The arm and leg are involved; close-up view; the patient is female:
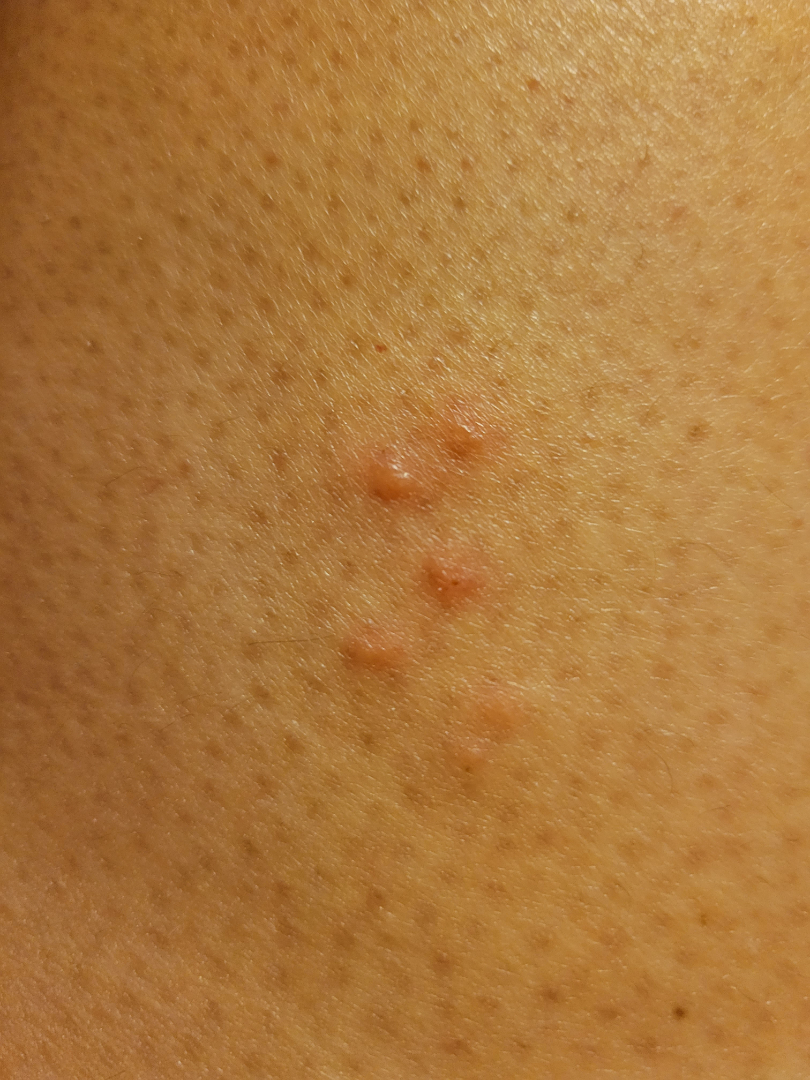Q: Any systemic symptoms?
A: fatigue
Q: Duration?
A: less than one week
Q: How does the lesion feel?
A: raised or bumpy
Q: What symptoms does the patient report?
A: itching and burning
Q: How does the patient describe it?
A: a rash
Q: What conditions are considered?
A: the impression was split between Folliculitis and Insect Bite; a more distant consideration is Allergic Contact Dermatitis; less likely is Herpes Simplex